A skin lesion imaged with a dermatoscope: 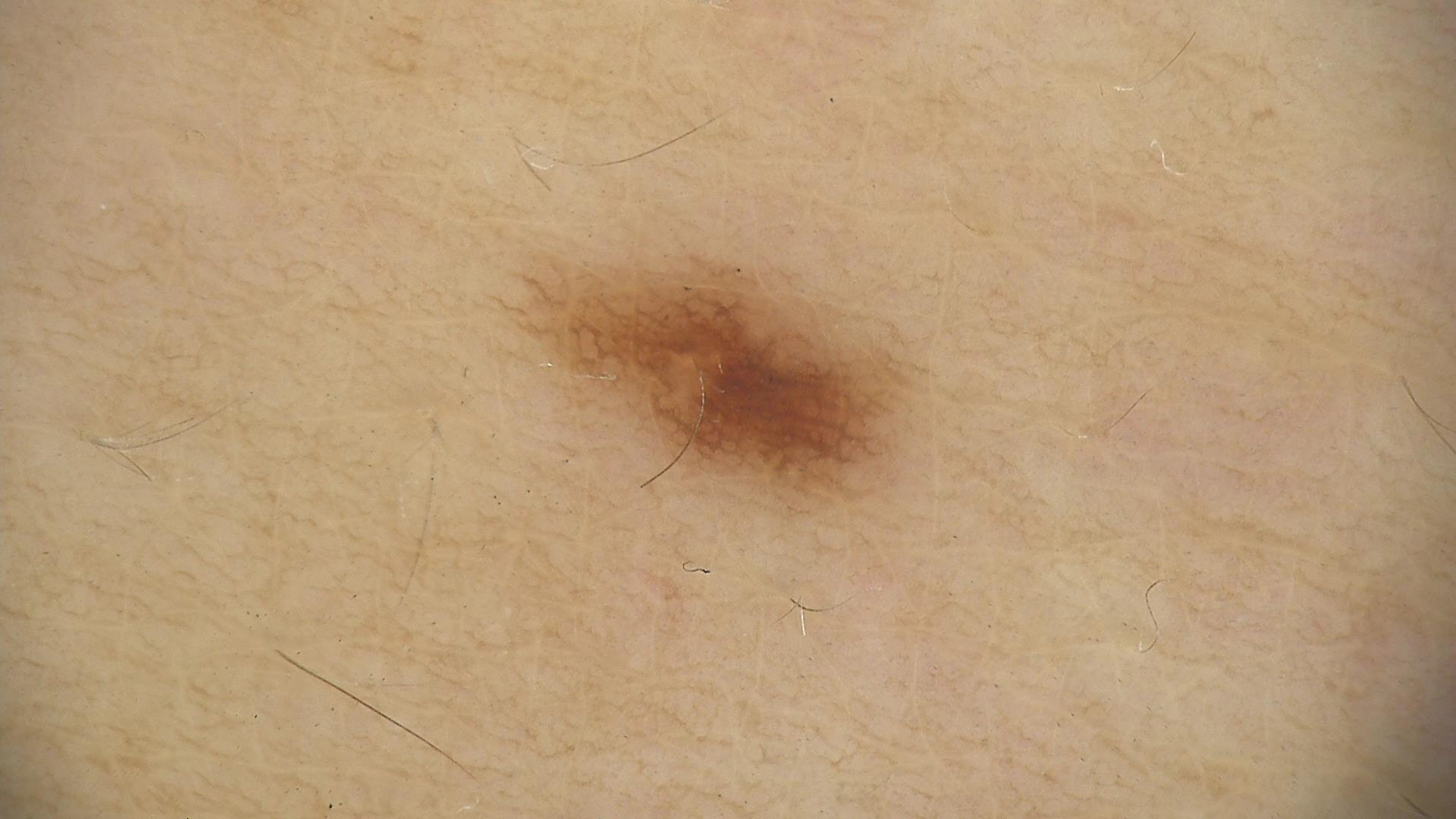The diagnostic label was a benign lesion — a dysplastic junctional nevus.